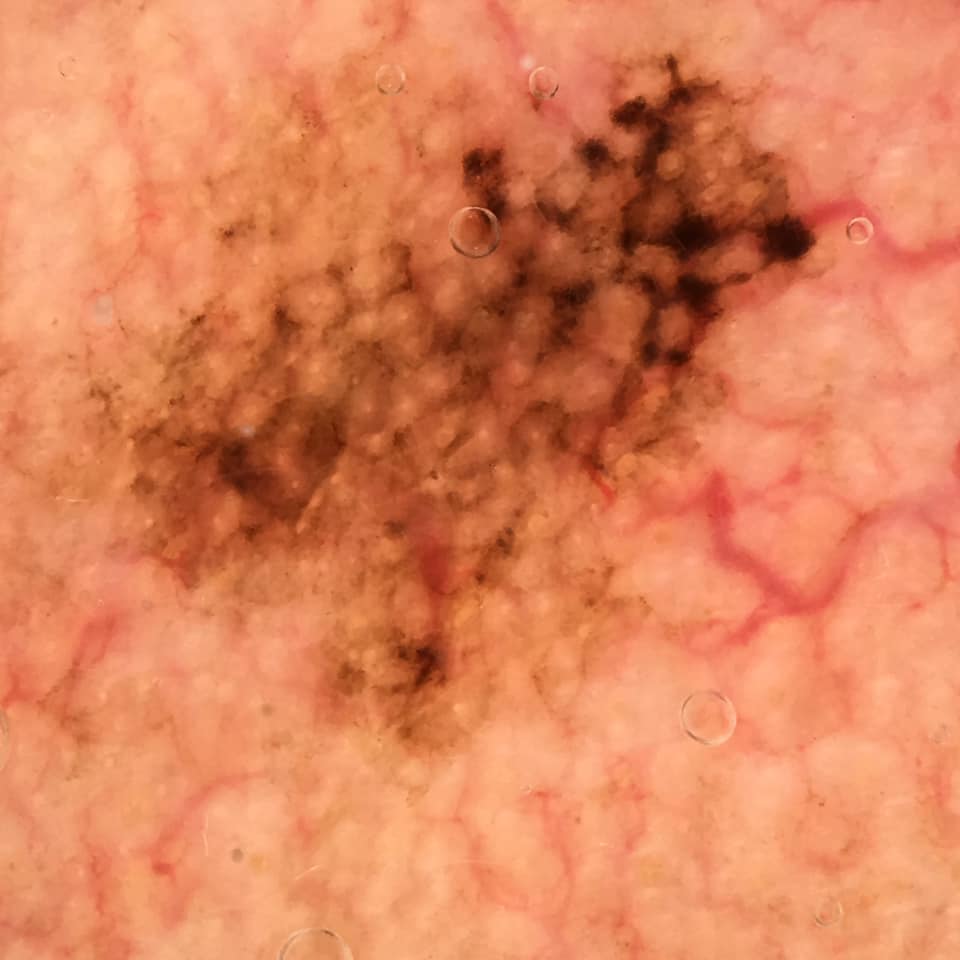imaging: dermoscopy
pathology: lentigo maligna (biopsy-proven)